The lesion involves the arm. The photograph was taken at a distance: 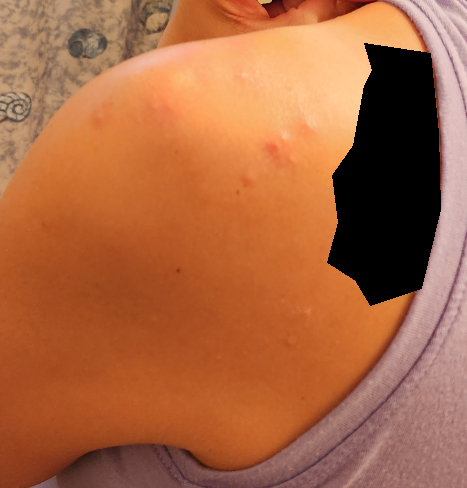Findings:
* assessment · ungradable on photographic review